The patient reports a personal history of cancer and a personal history of skin cancer; the patient says their skin reddens with sun exposure; the patient describes having a moderate number of moles; a dermoscopic image of a skin lesion — 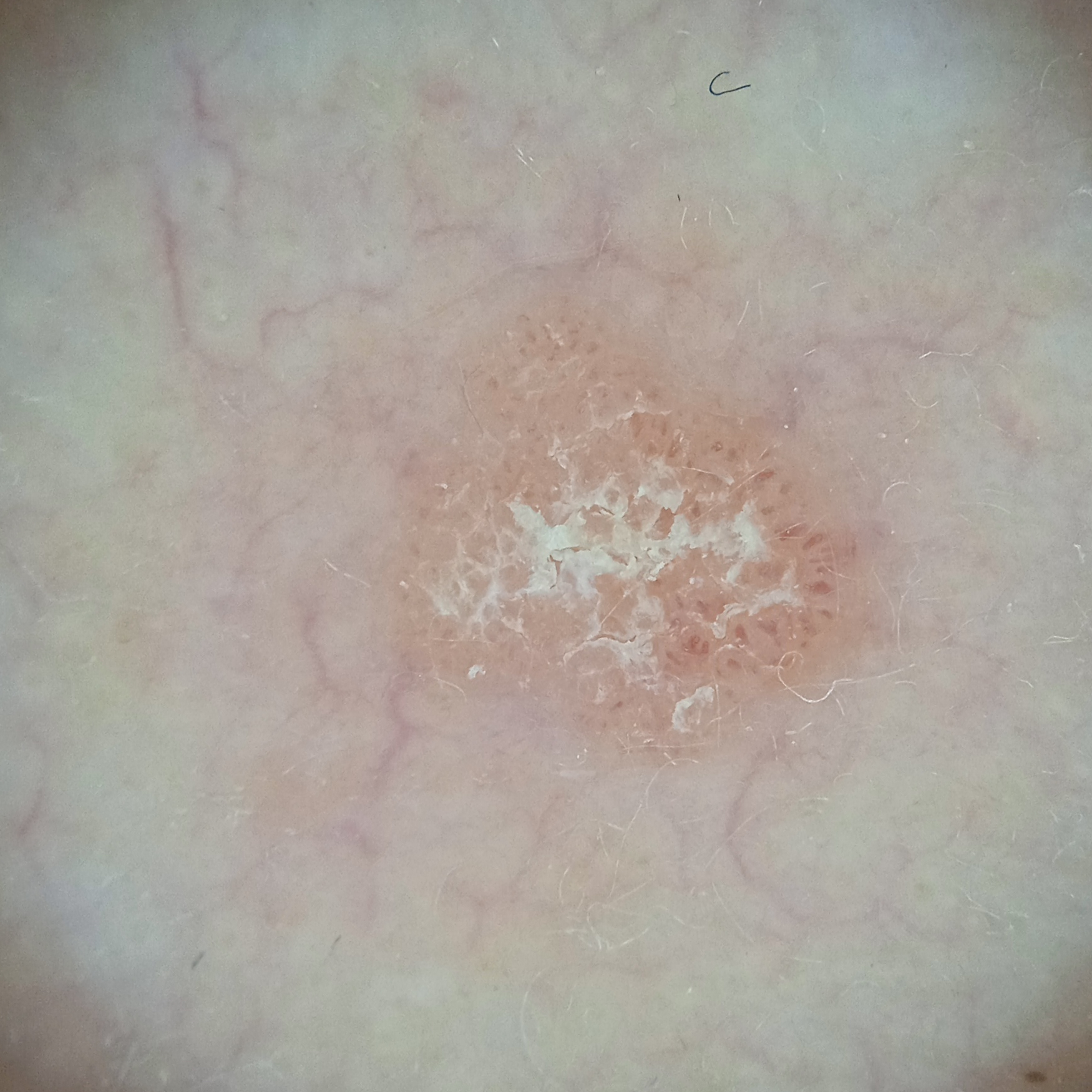The lesion involves the face. Measuring roughly 4.3 mm. The diagnostic impression was an actinic keratosis.